The patient says their skin tans without first burning; the patient describes having a moderate number of moles; a male patient 72 years old:
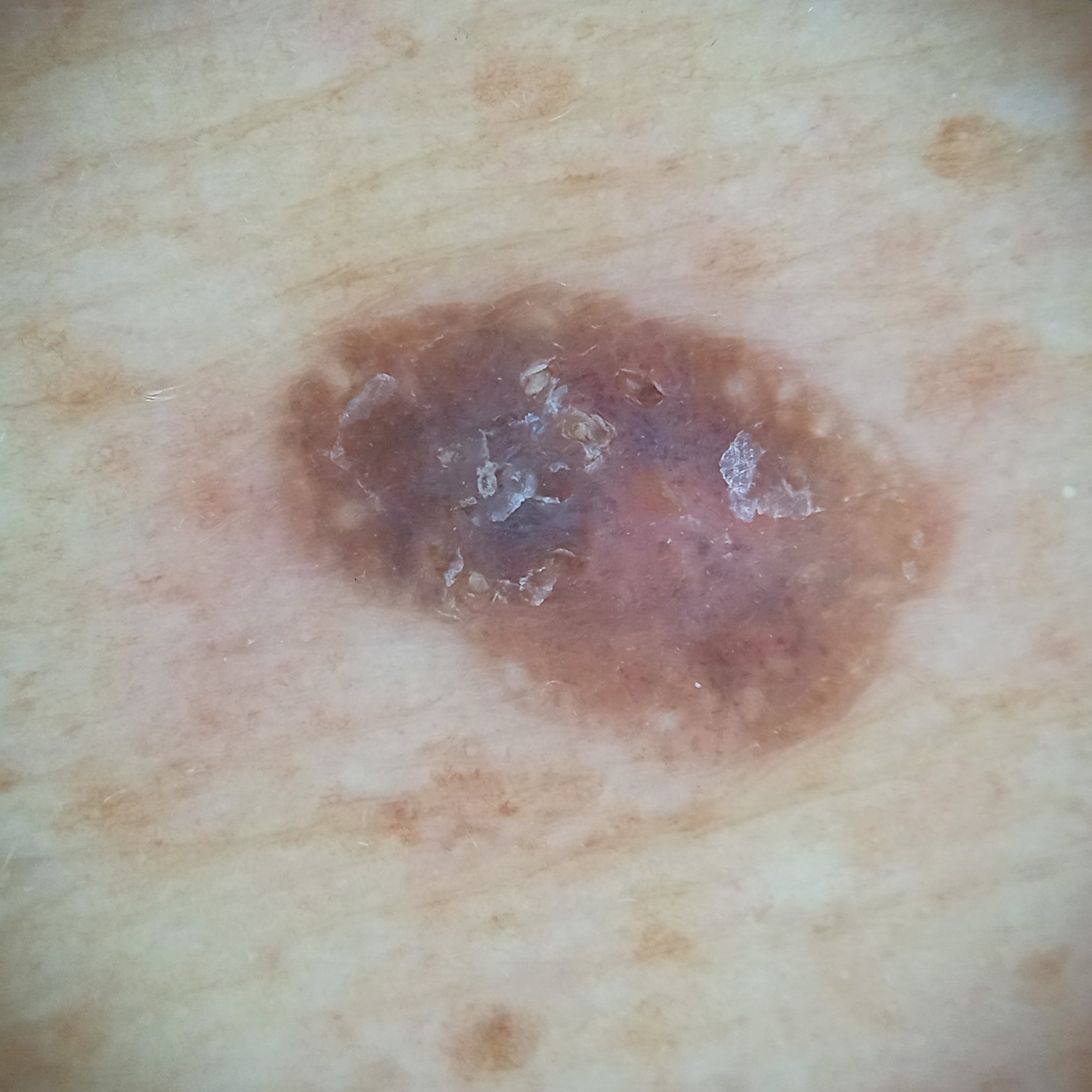Clinical context:
The lesion is located on the back. The lesion measures approximately 8.1 mm.
Assessment:
The diagnostic impression was a seborrheic keratosis.